Located on the back of the hand · associated systemic symptoms include joint pain and fatigue · the patient is 30–39, female · reported lesion symptoms include bothersome appearance, itching, pain, enlargement and burning · the patient indicates the condition has been present for less than one week · an image taken at a distance:
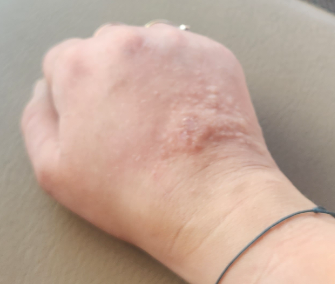diagnostic considerations — one reviewing dermatologist: most likely Eczema; also raised was Irritant Contact Dermatitis; lower on the differential is Allergic Contact Dermatitis.